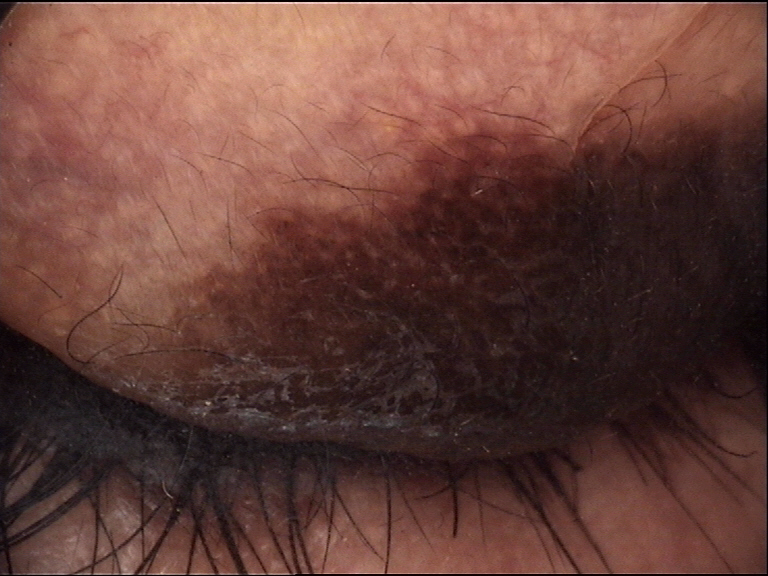Summary: A skin lesion imaged with a dermatoscope. The morphology is that of a banal lesion. Impression: Diagnosed as a congenital compound nevus.